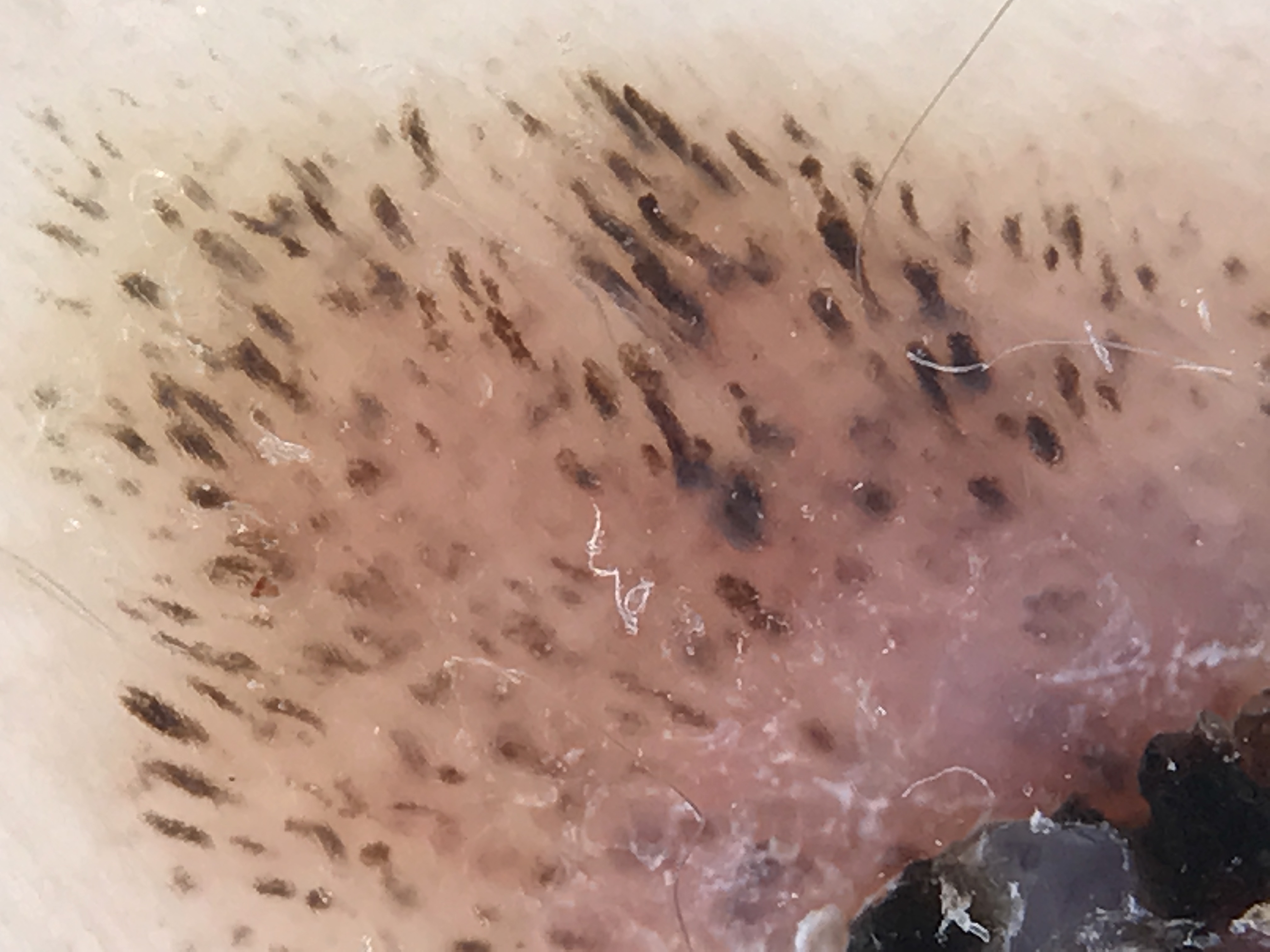Labeled as a congenital dysplastic compound nevus.